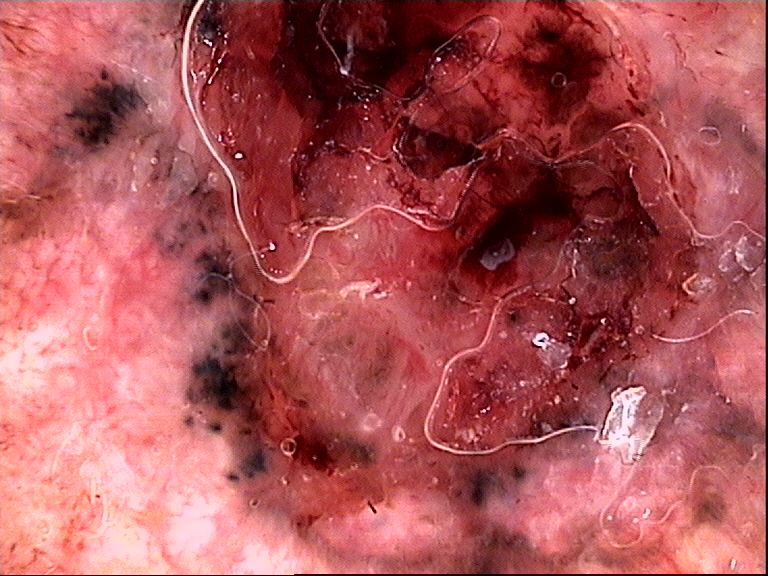Biopsy-confirmed as a basal cell carcinoma.